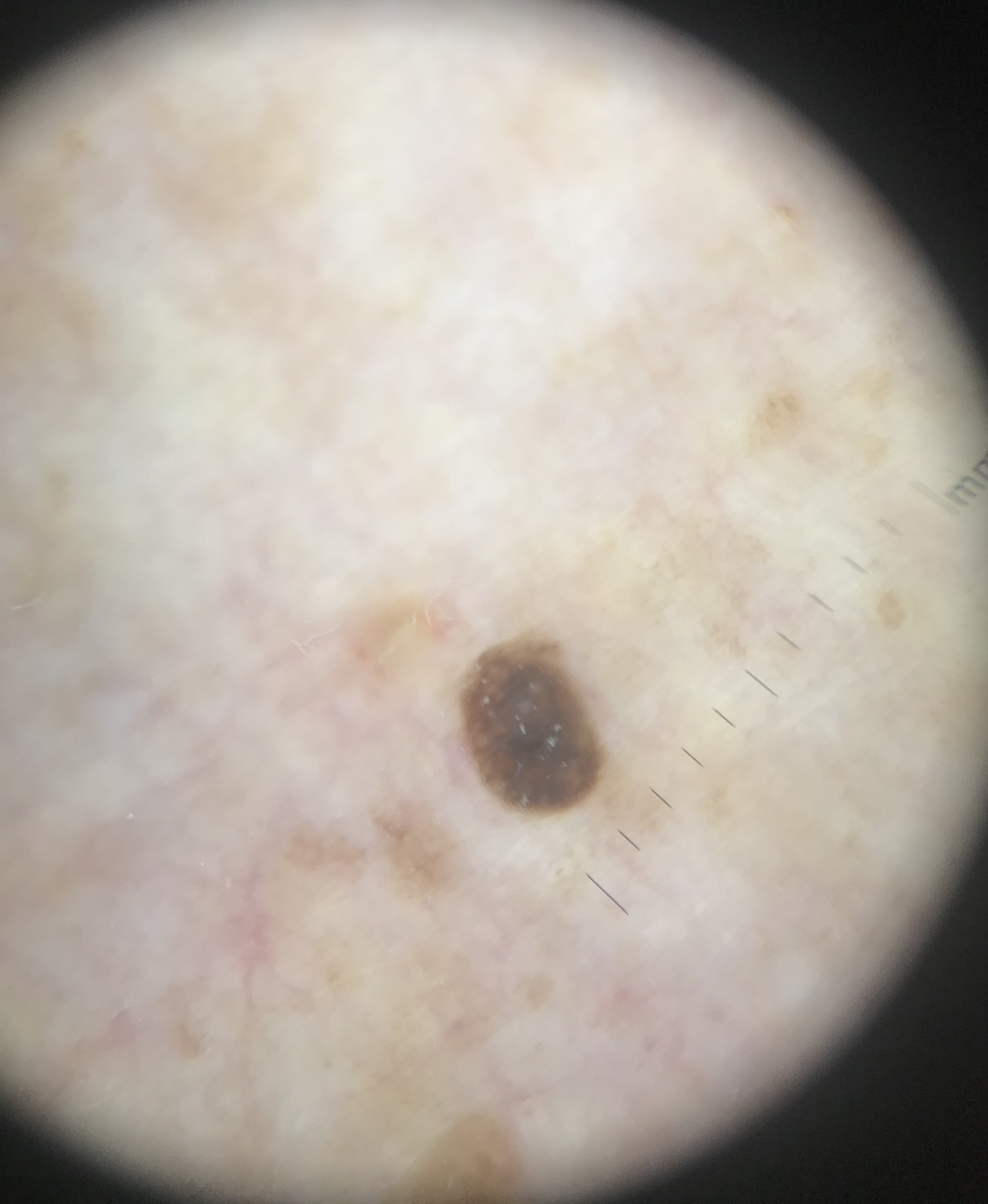Findings:
A skin lesion imaged with a dermatoscope. The architecture is that of a keratinocytic lesion.
Conclusion:
The diagnosis was a seborrheic keratosis.